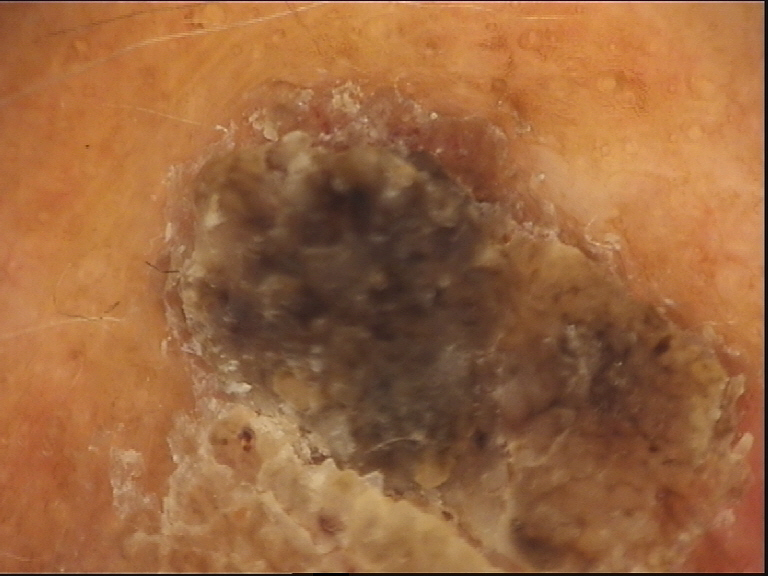{
  "image": "dermatoscopy",
  "diagnosis": {
    "name": "seborrheic keratosis",
    "code": "sk",
    "malignancy": "benign",
    "super_class": "non-melanocytic",
    "confirmation": "expert consensus"
  }
}